The affected area is the leg; a close-up photograph; the subject is a male aged 40–49 — 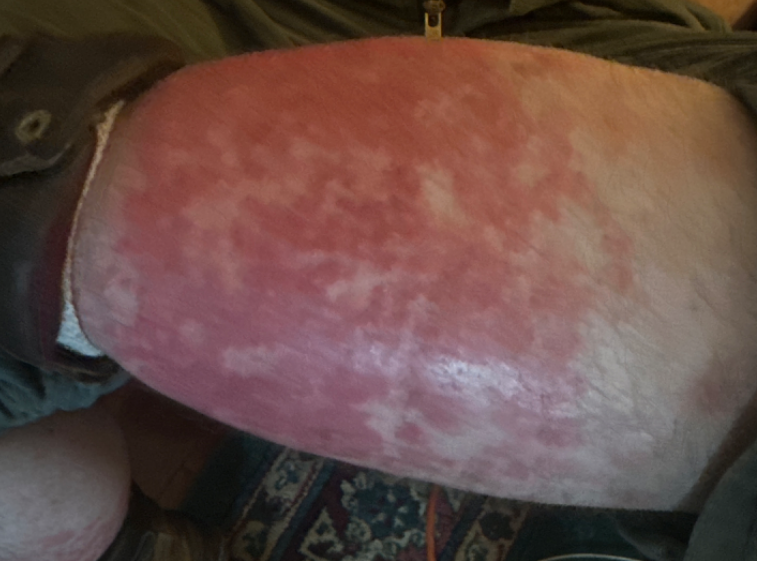assessment=could not be assessed; other reported symptoms=fatigue; patient-reported symptoms=darkening, enlargement, bothersome appearance and pain; skin tone=self-reported Fitzpatrick phototype III; duration=less than one week; self-categorized as=a rash; lesion texture=raised or bumpy.